Collected as part of a research study, without a referral diagnosis · the patient describes having few moles overall · the patient says their skin tans without first burning · a female patient 84 years old:
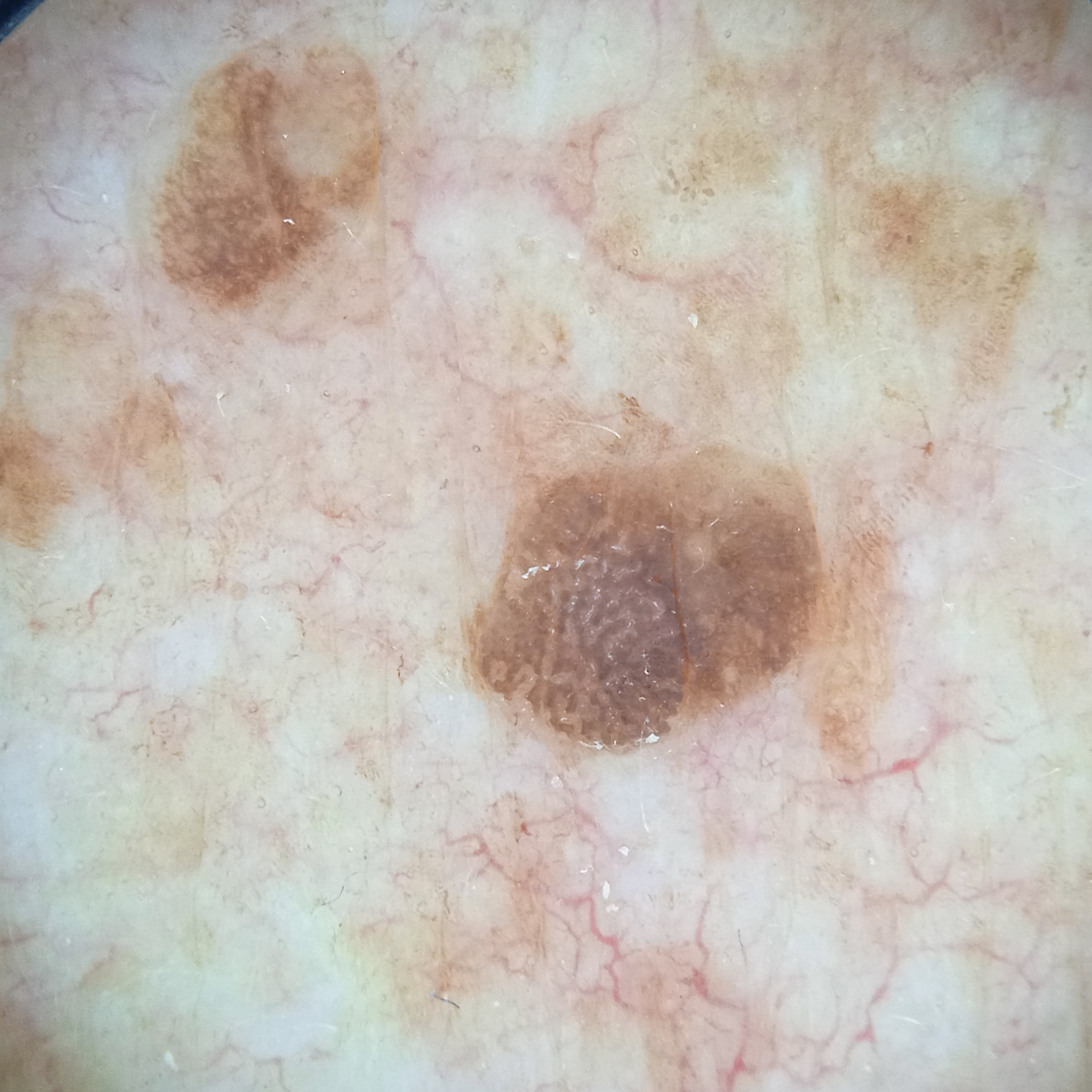diameter — 4.6 mm
diagnostic label — seborrheic keratosis (dermatologist consensus)